The lesion involves the leg, the subject is female, the photo was captured at an angle: 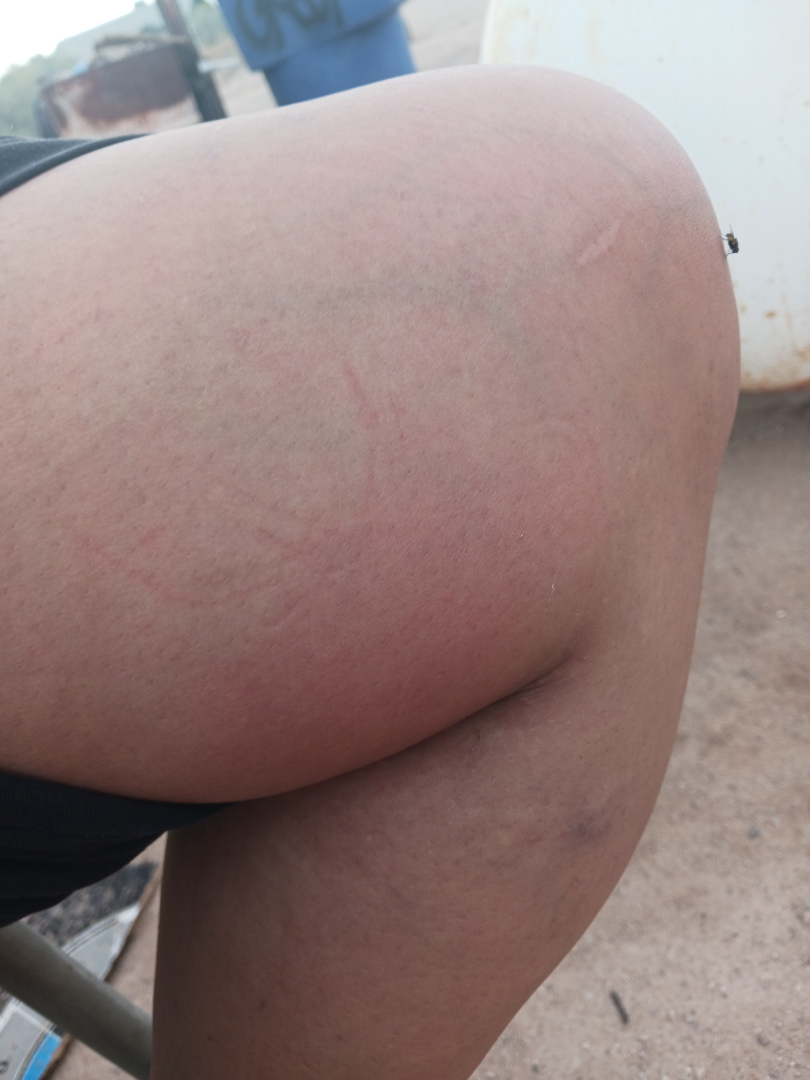Skin tone: Fitzpatrick II; non-clinician graders estimated Monk skin tone scale 2 or 4 (two reviewer pools disagreed). The lesion is described as fluid-filled. Self-categorized by the patient as acne. On remote review of the image, the differential, in no particular order, includes Cellulitis and Eczema; a remote consideration is Insect Bite; less likely is deep vein thrombosis.